Close-up view · FST V; lay graders estimated Monk skin tone scale 4 or 5:
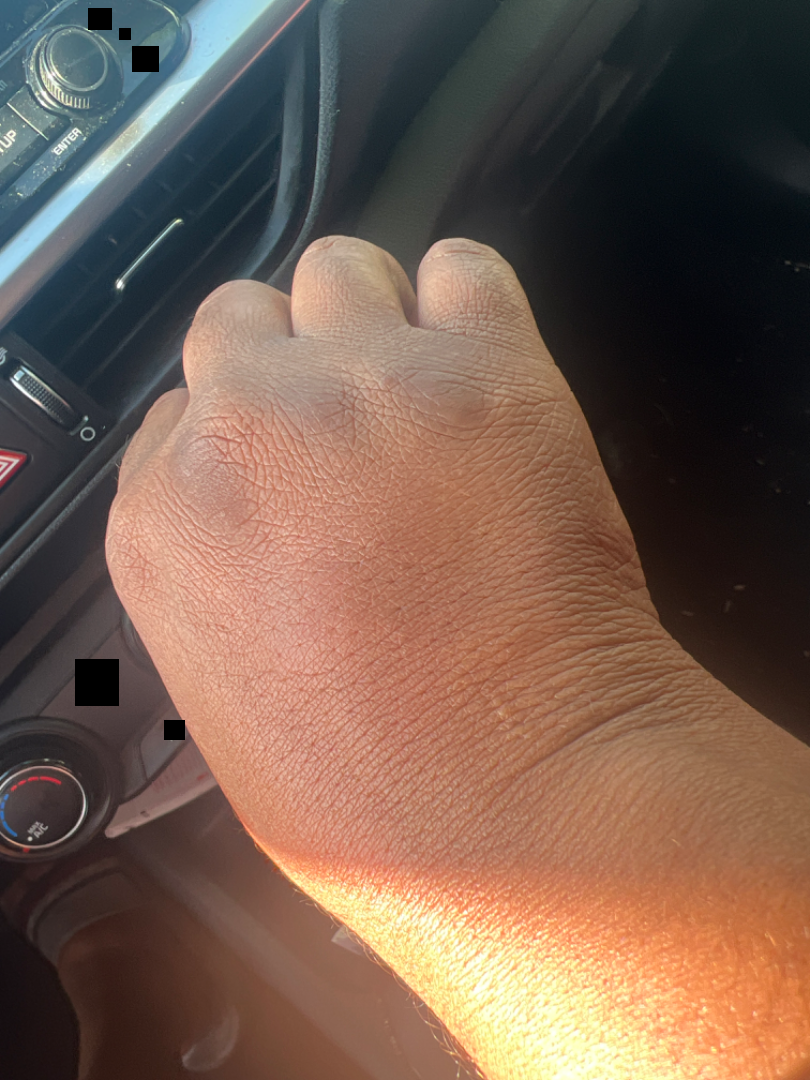assessment: in keeping with Knuckle pads.